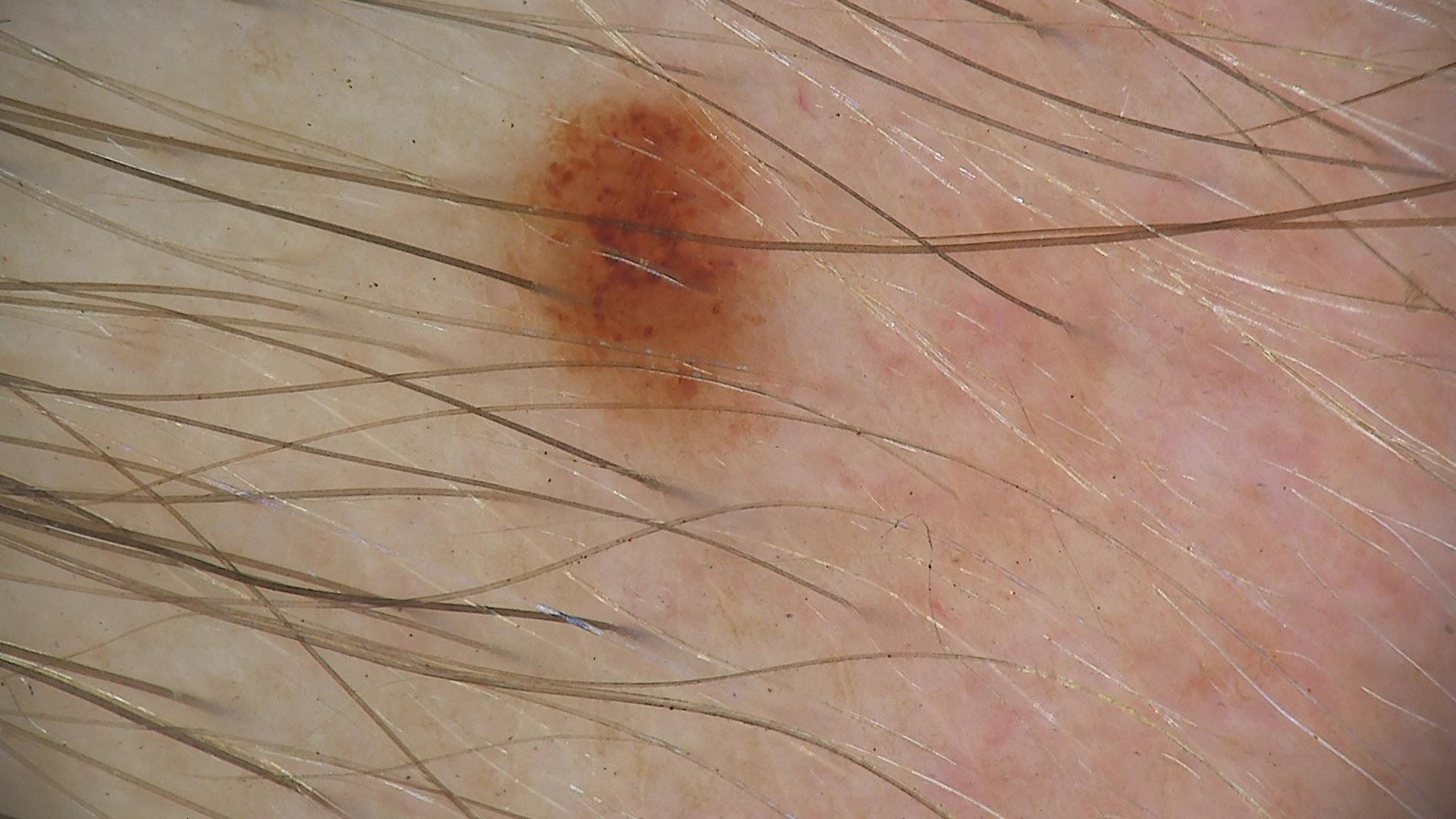imaging: dermatoscopy; assessment: compound nevus (expert consensus).